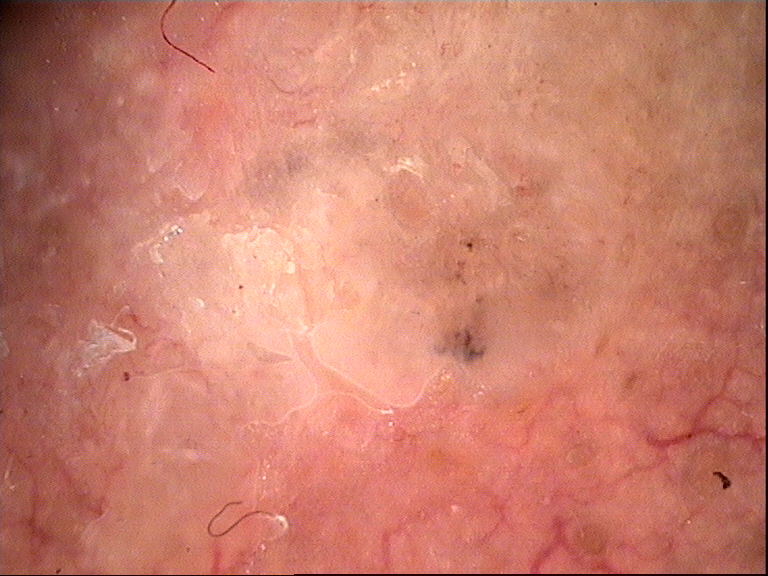A dermoscopic photograph of a skin lesion.
Histopathologically confirmed as a squamous cell carcinoma.